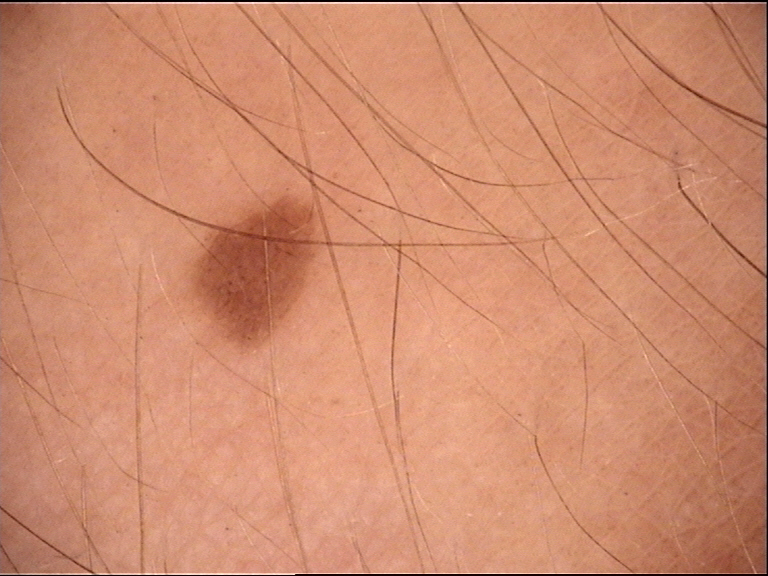Conclusion:
Diagnosed as a junctional nevus.